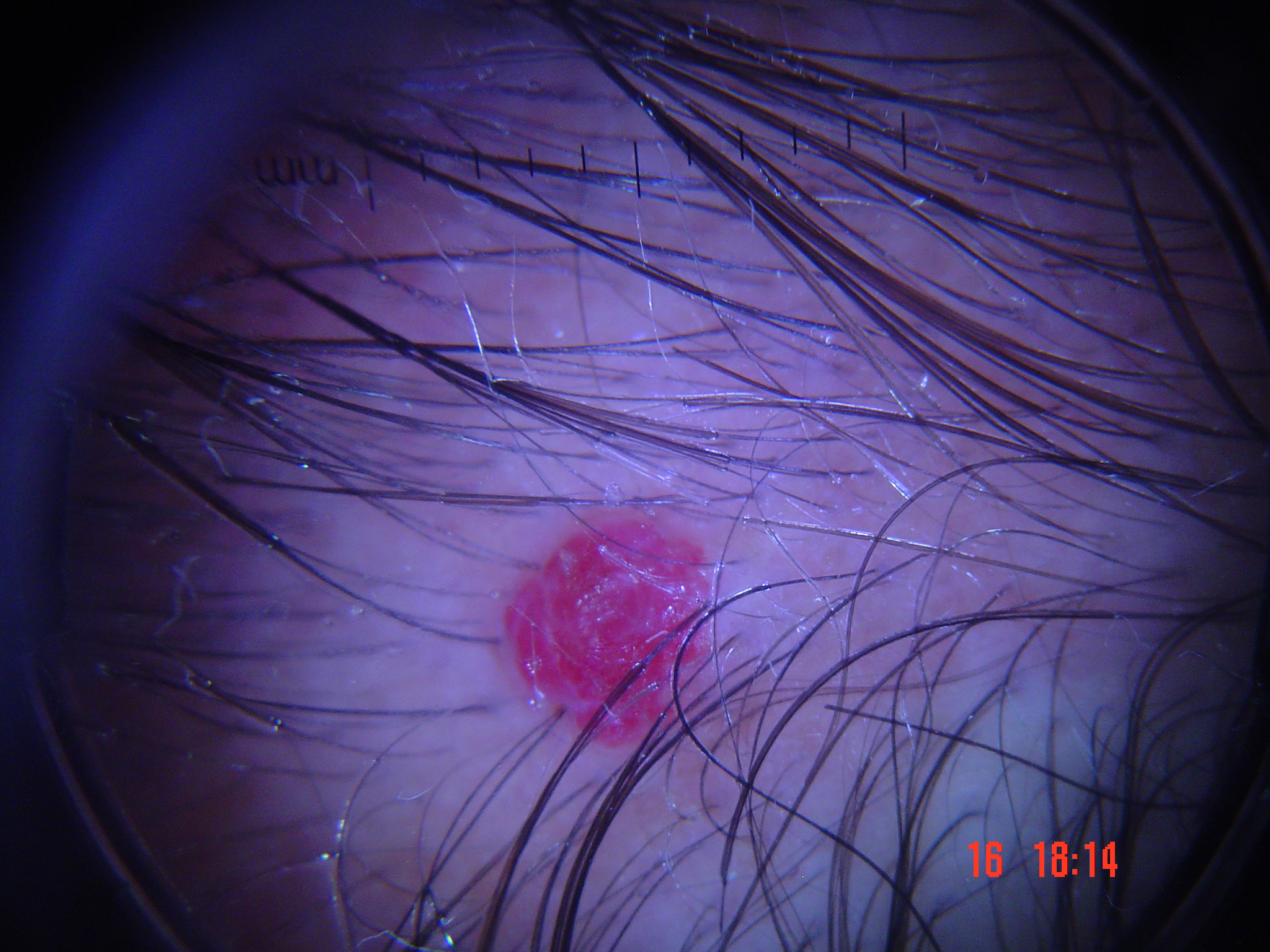Diagnosed as a hemangioma.